The photograph is a close-up of the affected area; female patient, age 60–69; located on the head or neck: 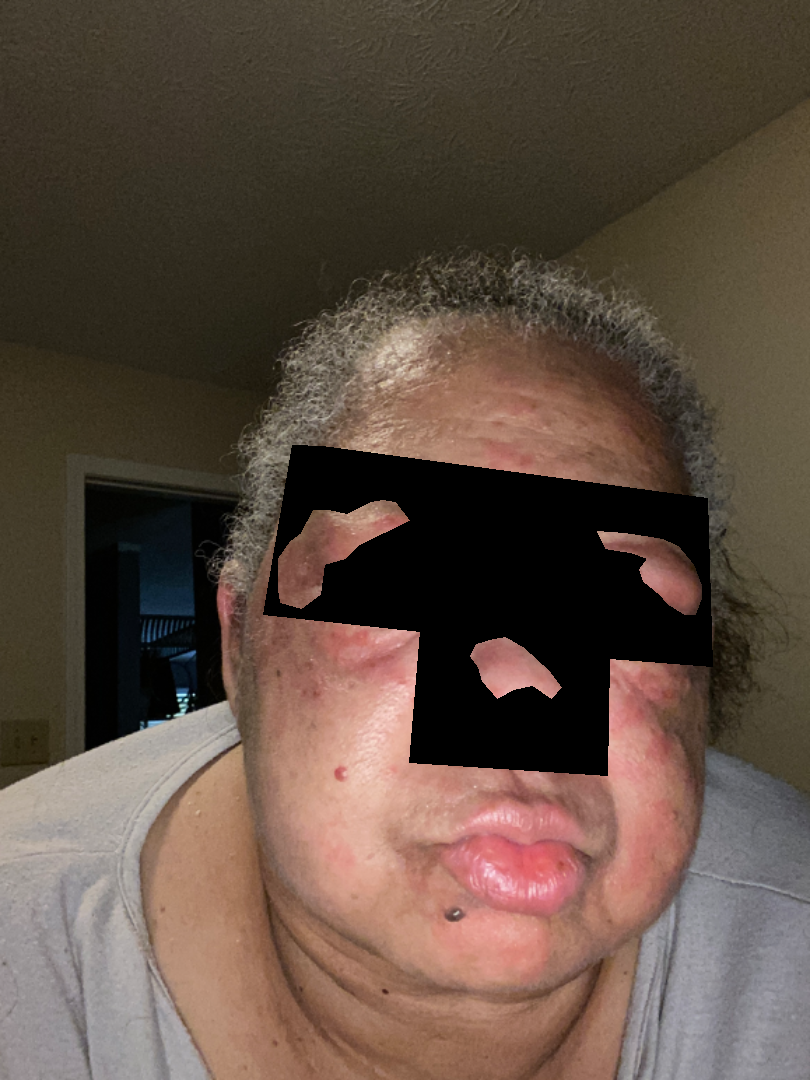impression = three dermatologists each reviewed the case: the differential is split between Seborrheic Dermatitis and Eczema; a more distant consideration is Cutaneous lupus; less likely is Allergic Contact Dermatitis; less probable is Rosacea